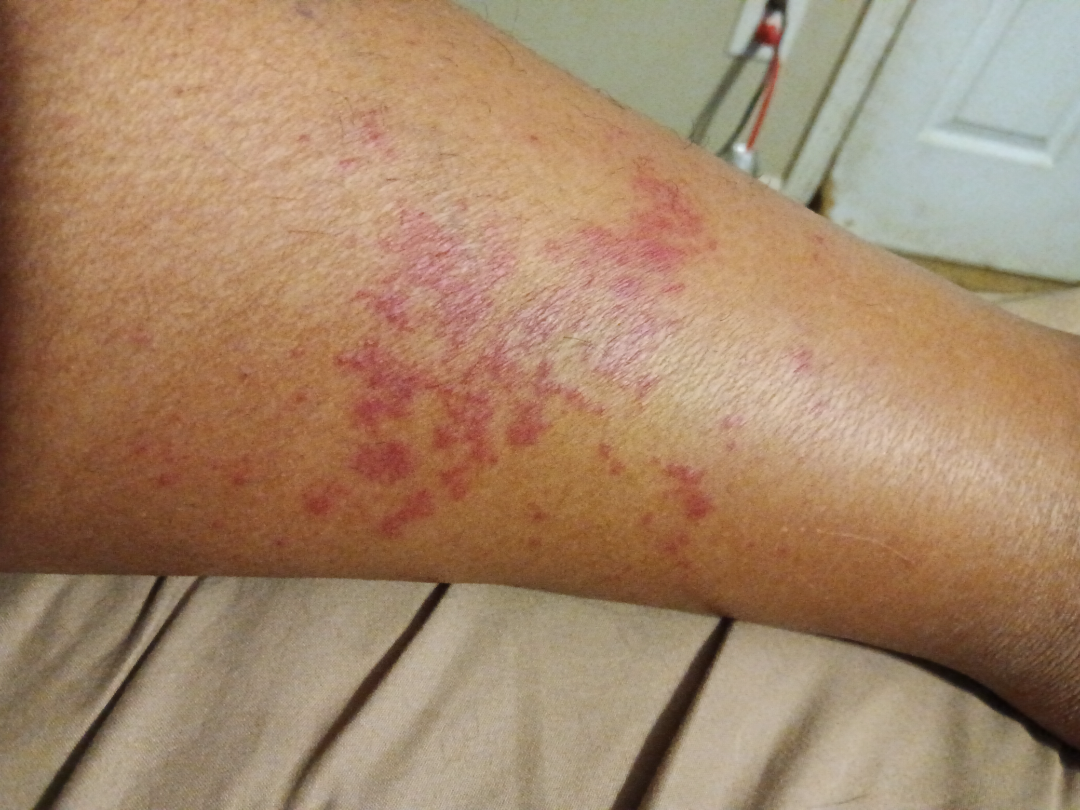Close-up view.
On photographic review: the impression was split between Purpura and Hemangioma; lower on the differential is Vasculitis of the skin.